Per the chart, a previous melanoma. A skin lesion imaged with contact-polarized dermoscopy. A male subject about 60 years old.
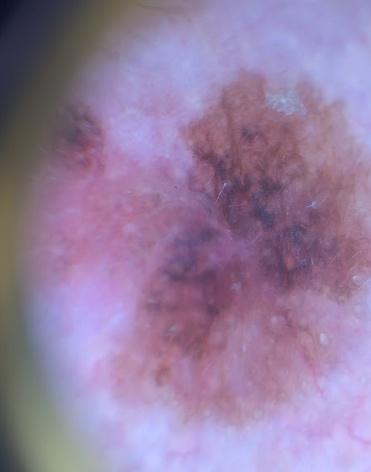Summary:
The lesion is on the head or neck.
Conclusion:
The biopsy diagnosis was a malignancy — a melanoma.